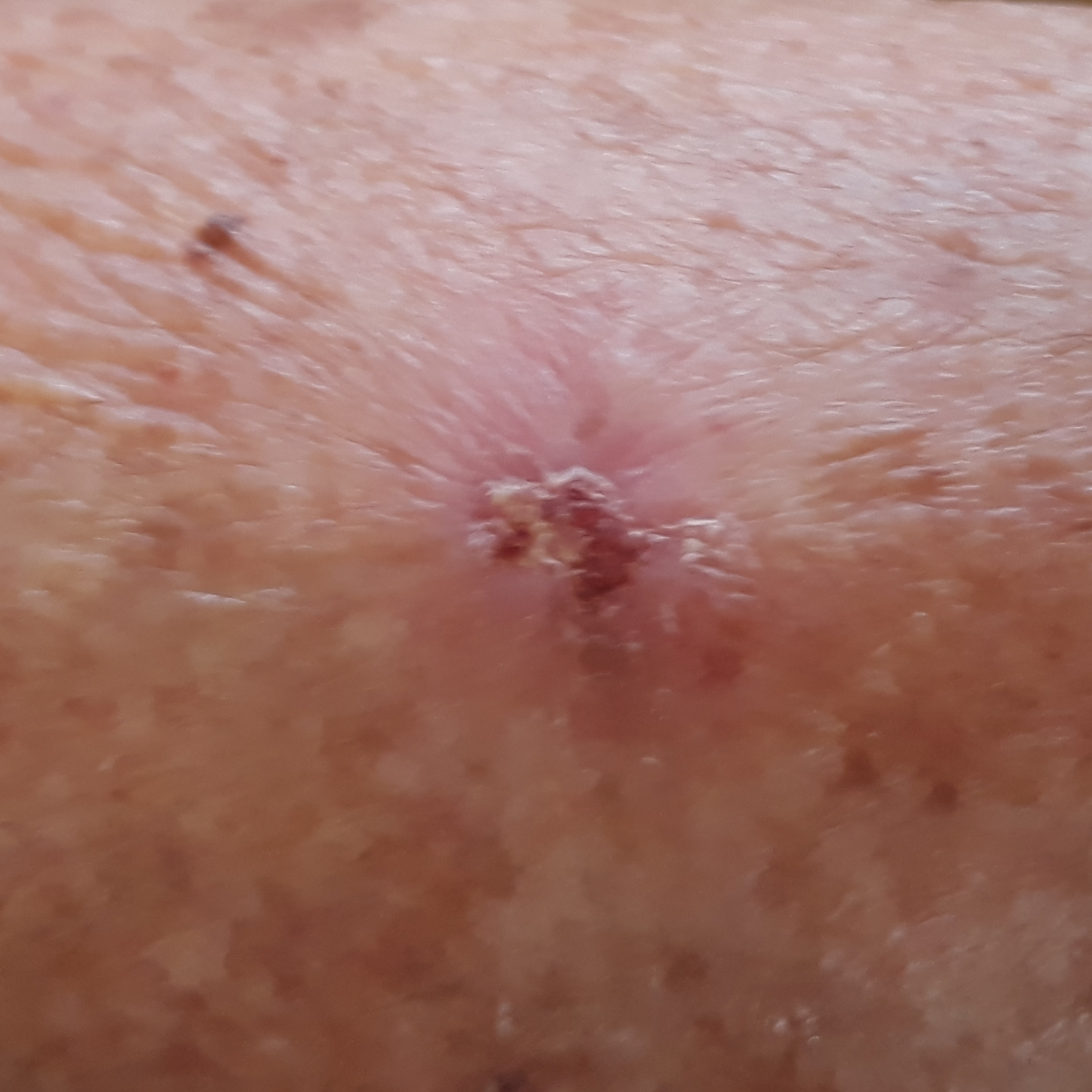skin phototype: III; imaging: smartphone clinical photo; exposures: prior malignancy (patient or family); patient: female, 78 years old; lesion size: approx. 8 × 6 mm; symptoms: itching, elevation, bleeding; diagnostic label: basal cell carcinoma (biopsy-proven).